A dermatoscopic image of a skin lesion:
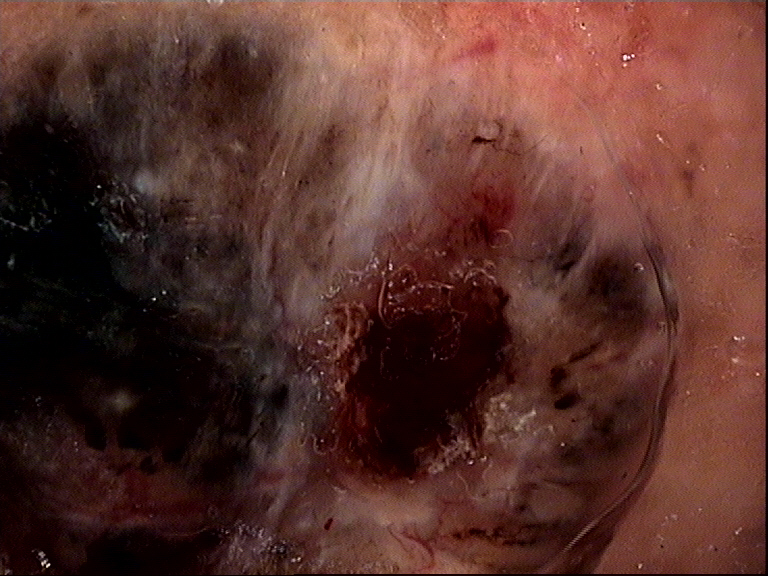The architecture is that of a keratinocytic lesion. Histopathology confirmed a basal cell carcinoma.